A dermoscopic image of a skin lesion.
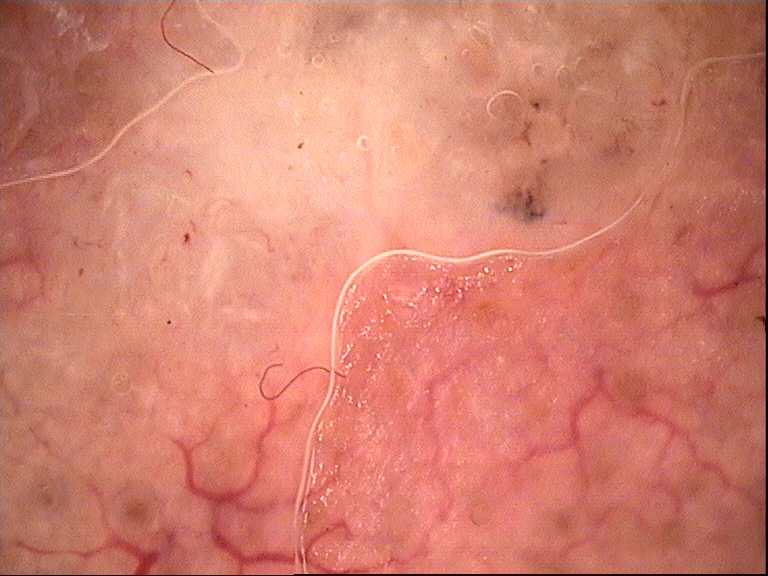Confirmed on histopathology as a keratinocytic lesion — a squamous cell carcinoma.